A dermatoscopic image of a skin lesion:
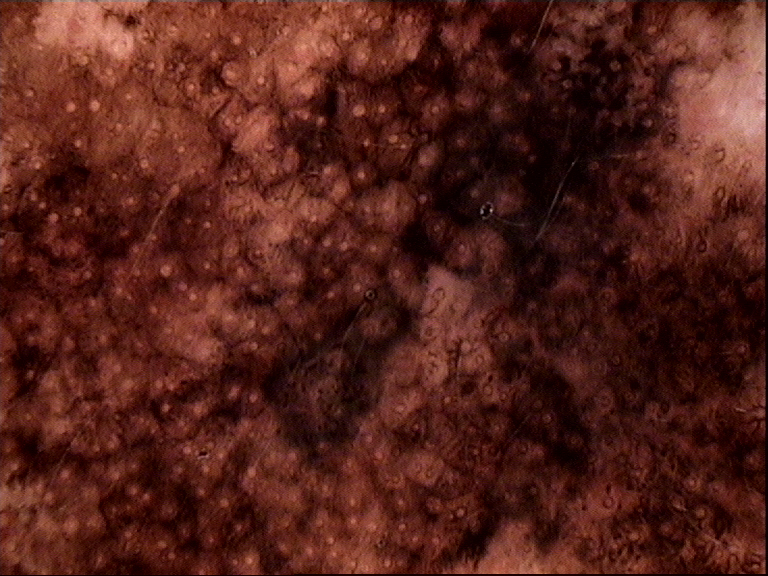The biopsy diagnosis was a lentigo maligna.